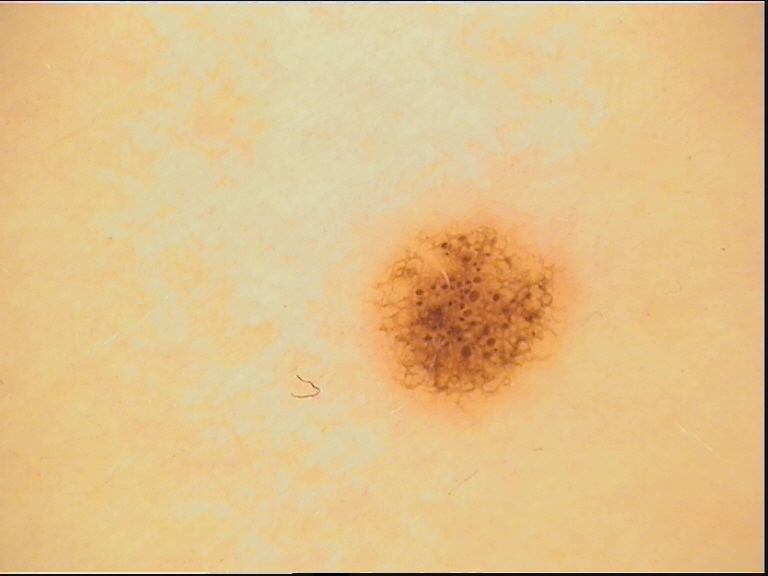| key | value |
|---|---|
| label | dysplastic junctional nevus (expert consensus) |